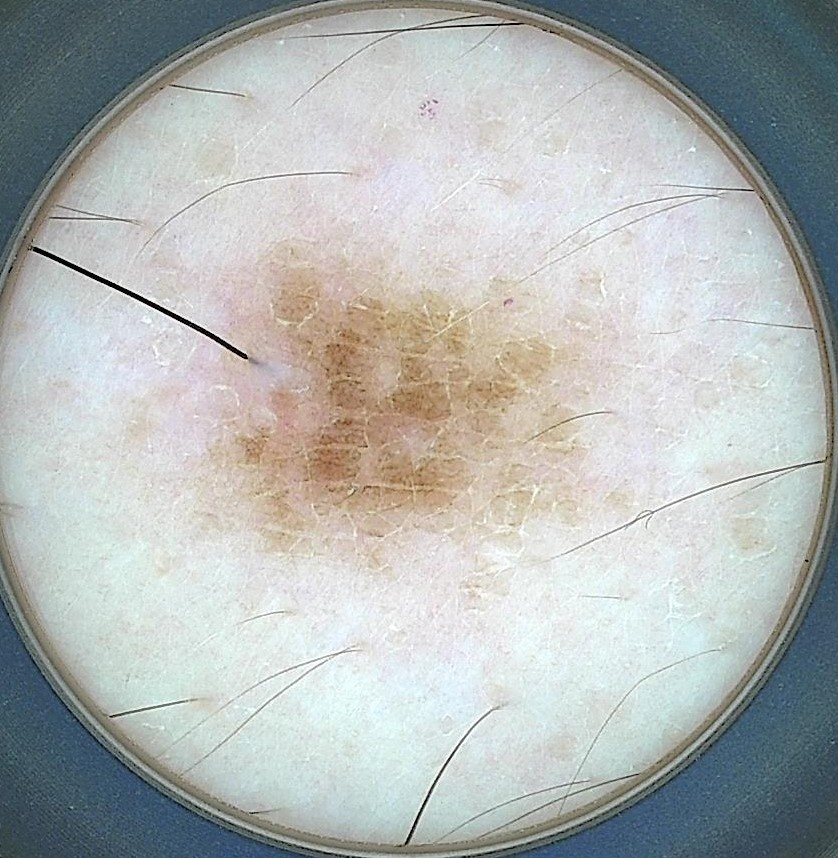Diagnosed as a dysplastic junctional nevus.